A dermoscopic photograph of a skin lesion: 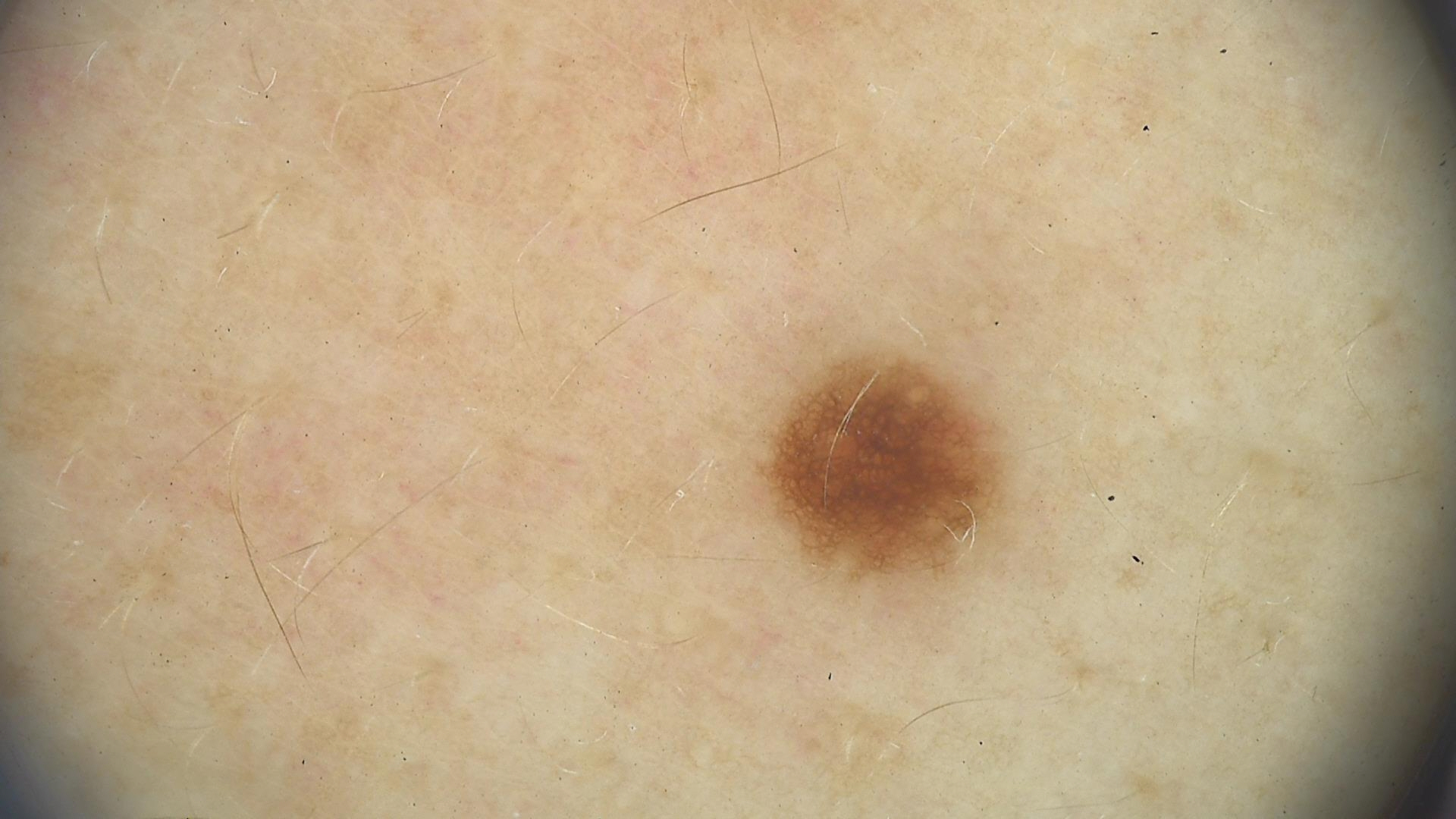| key | value |
|---|---|
| assessment | dysplastic junctional nevus (expert consensus) |